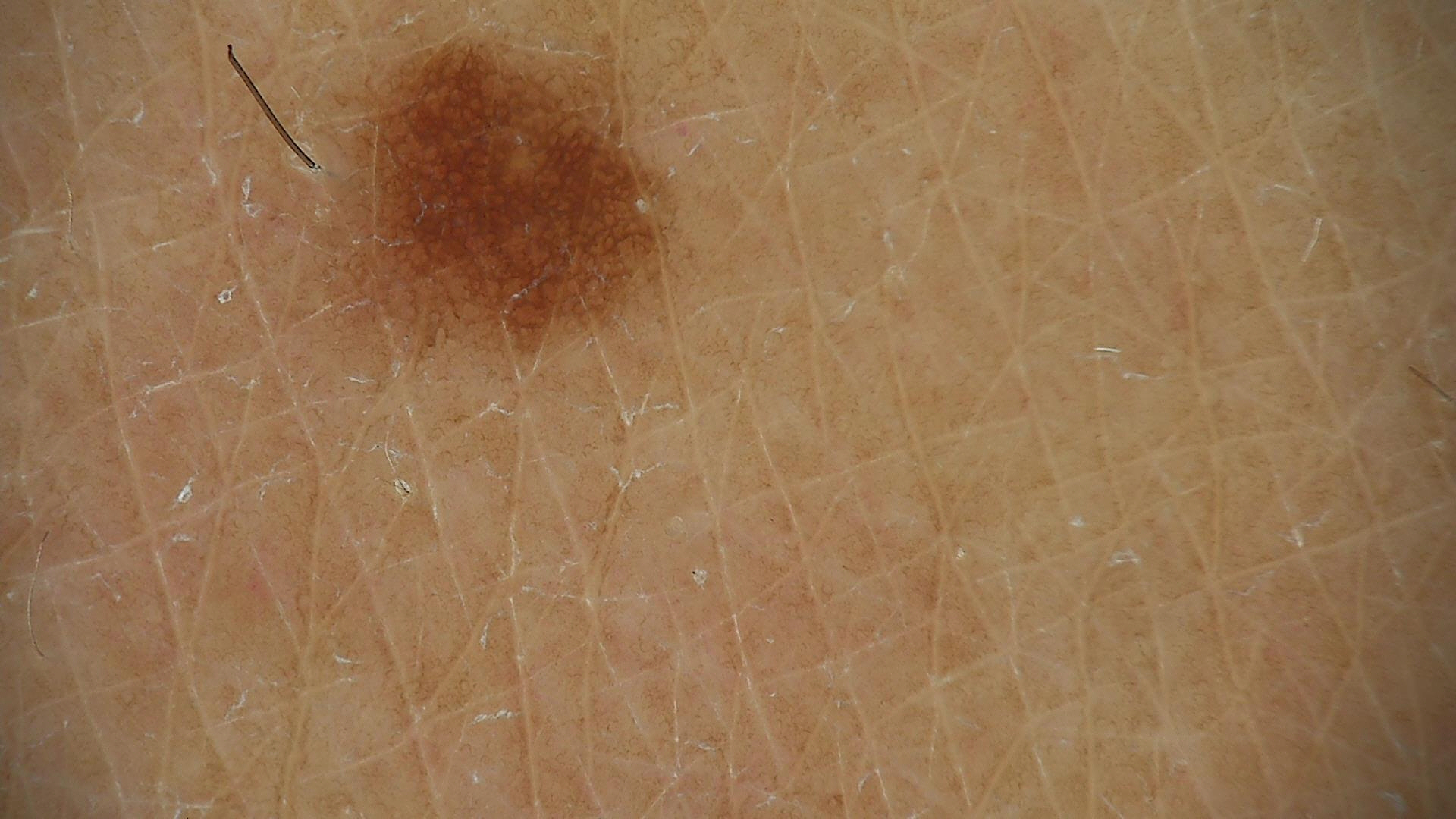diagnosis: dysplastic junctional nevus (expert consensus)